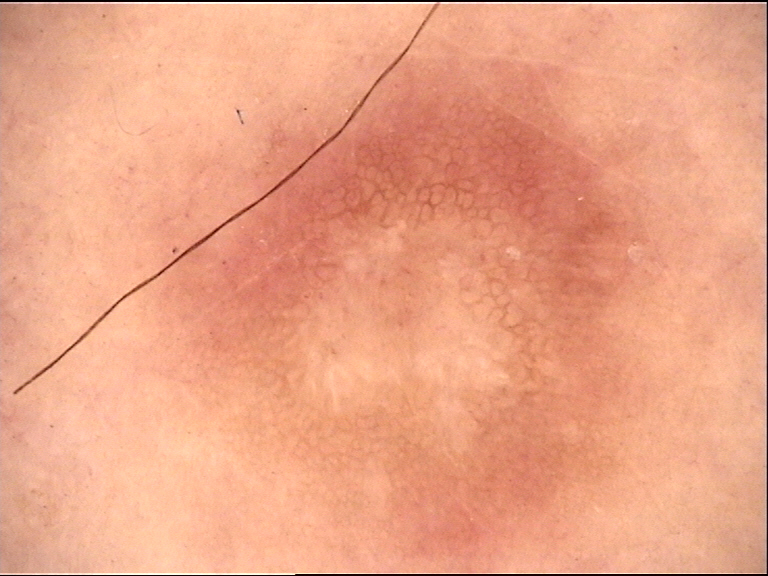Labeled as a dermatofibroma.